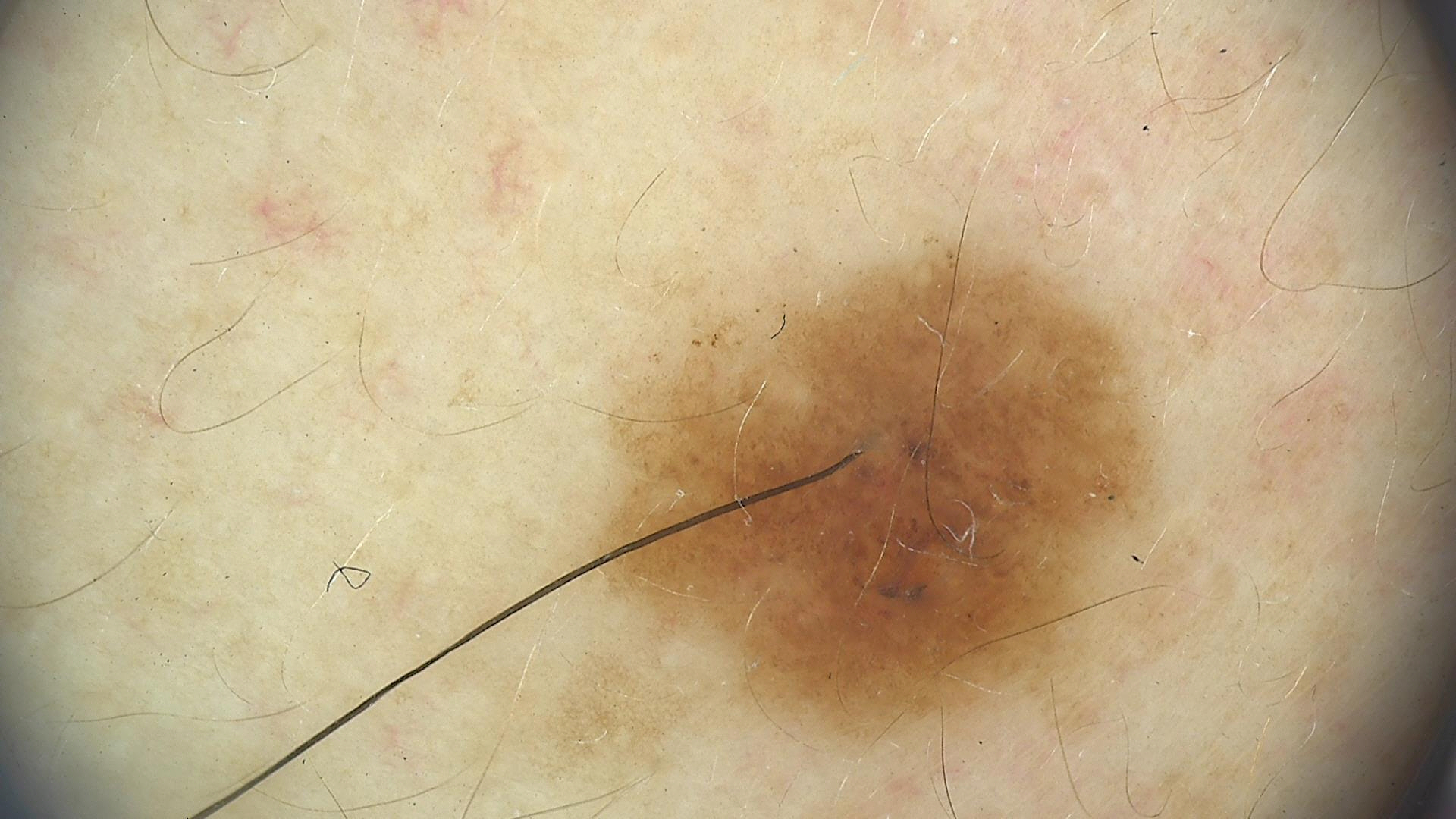Case:
A dermoscopy image of a single skin lesion.
Impression:
Diagnosed as a dysplastic junctional nevus.